The arm is involved; the photograph is a close-up of the affected area; the patient notes the condition has been present for less than one week:
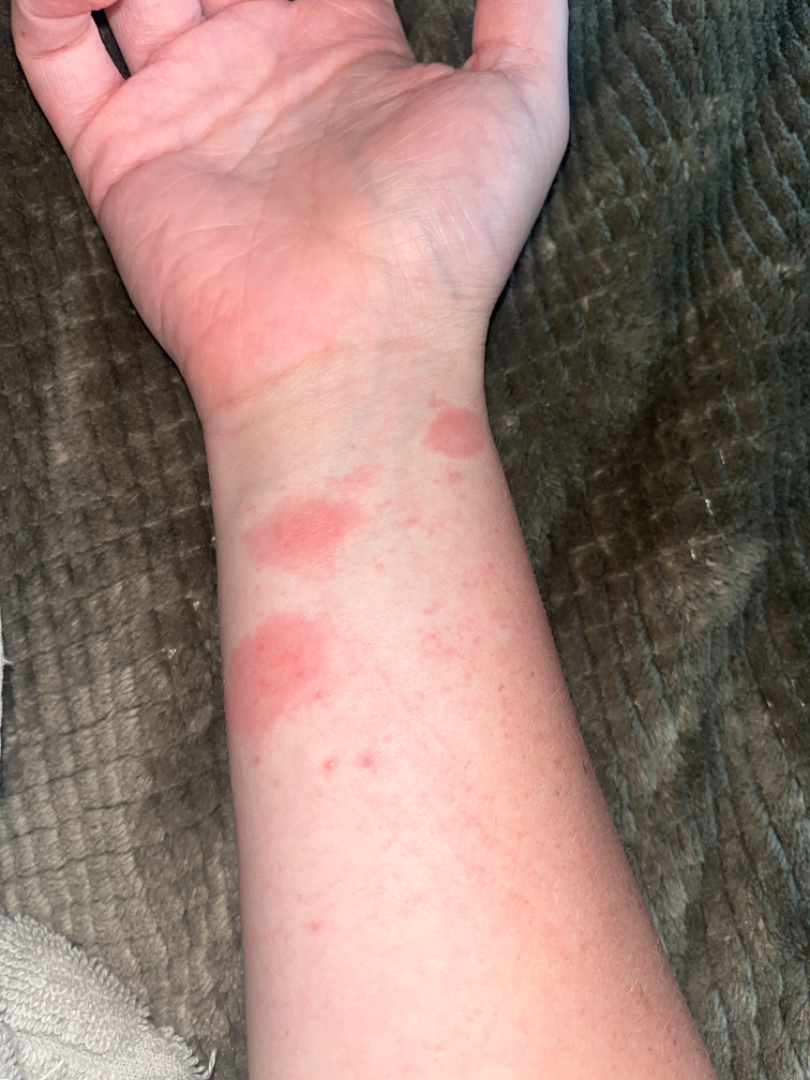On photographic review by a dermatologist, most likely Insect Bite; also consider Urticaria; less likely is Allergic Contact Dermatitis.